The patient is female, this is a close-up image, located on the leg — 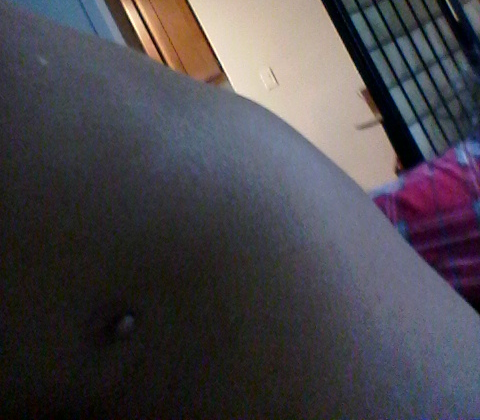Review:
The dermatologist could not determine a likely condition from the photograph alone.